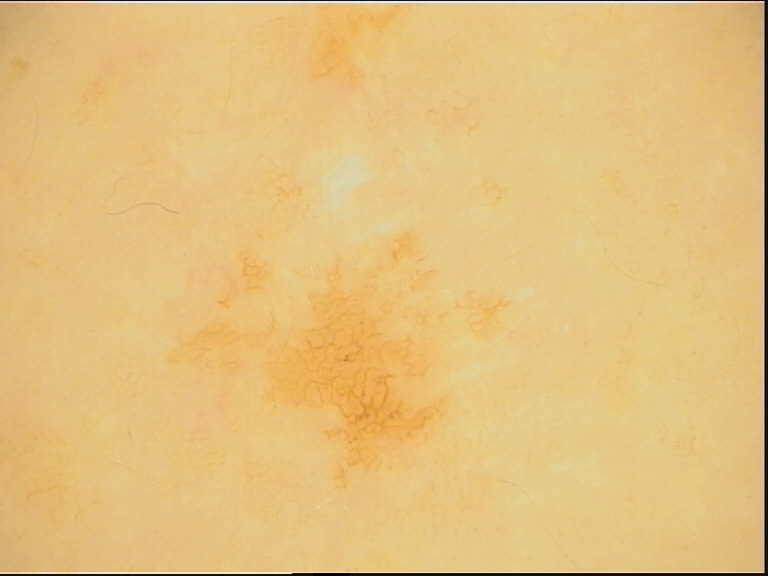A dermoscopic photograph of a skin lesion.
Consistent with a benign lesion — a lentigo simplex.